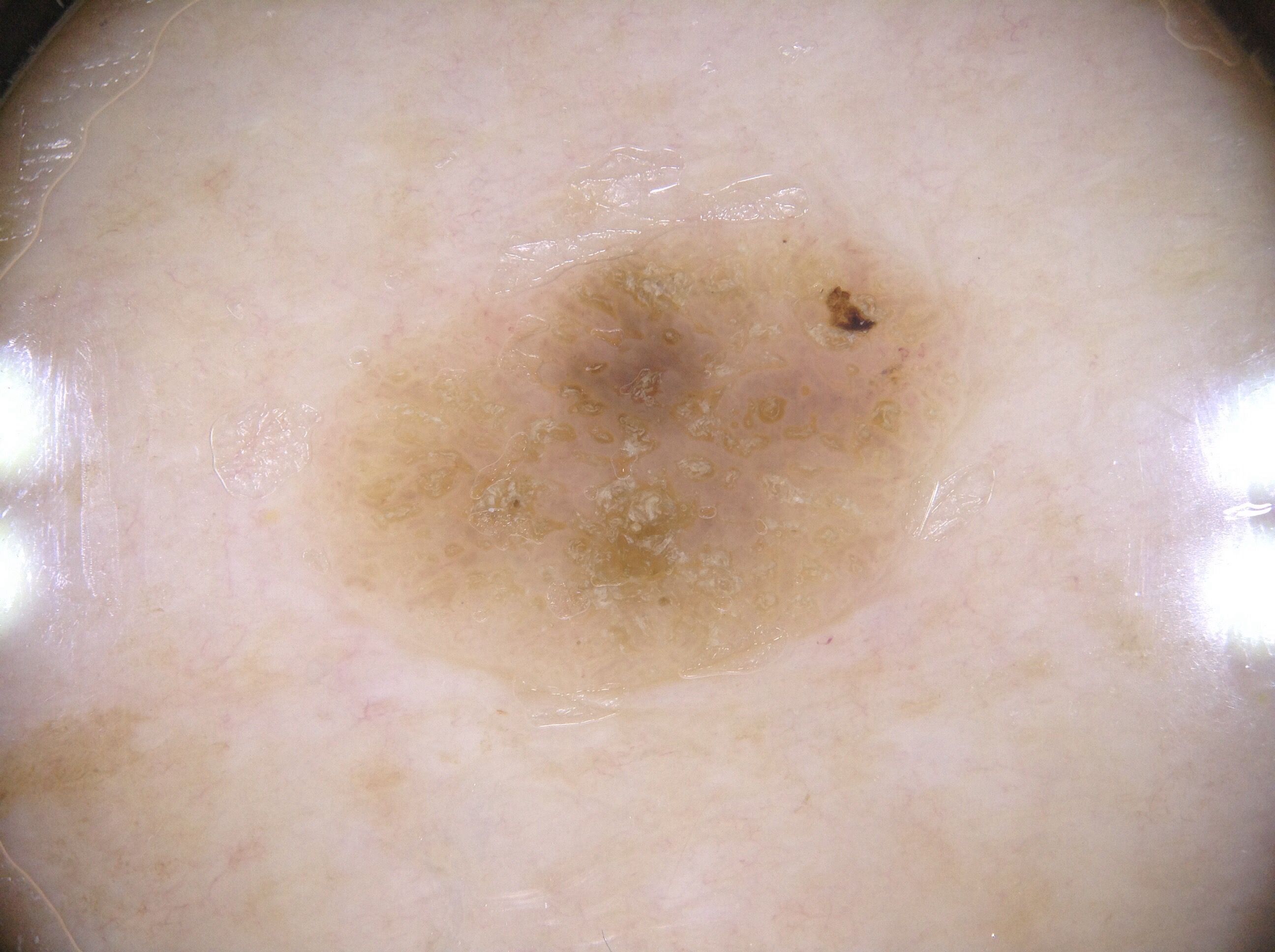Dermoscopy of a skin lesion.
The dermoscopic pattern shows milia-like cysts.
In (x1, y1, x2, y2) order, the visible lesion spans <box>339, 231, 956, 669</box>.
Diagnosed as a seborrheic keratosis, a benign lesion.